The lesion involves the leg · the photo was captured at an angle:
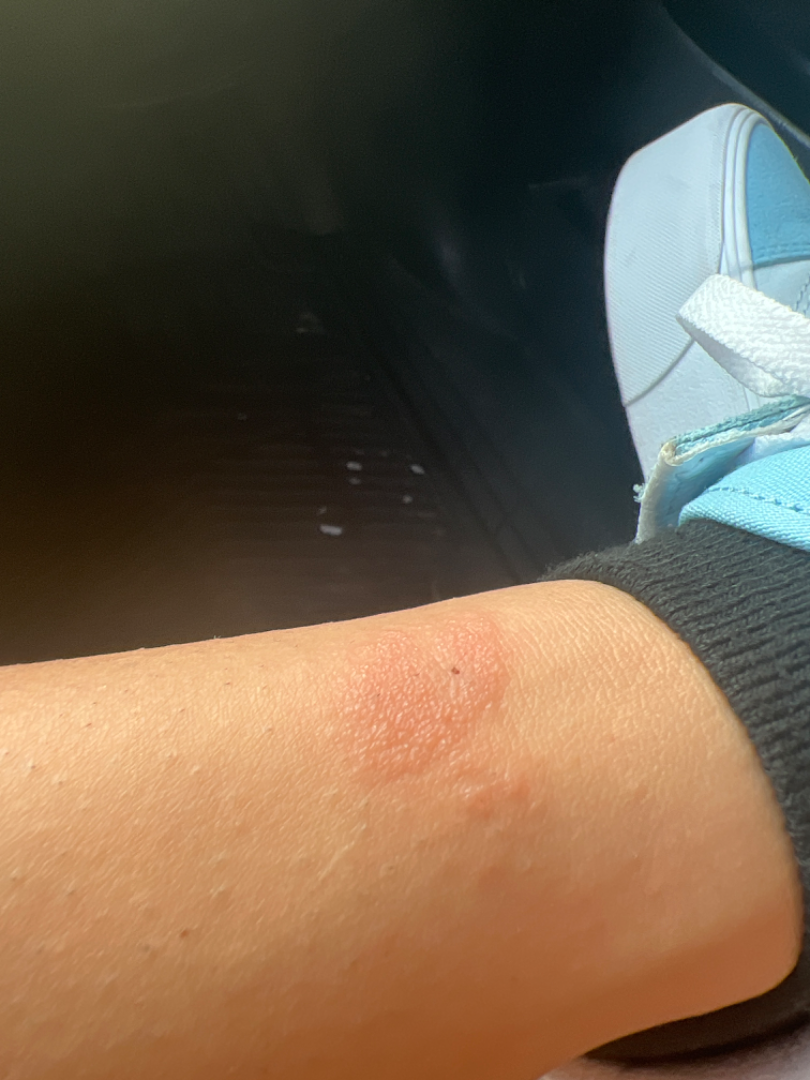present for=less than one week
self-categorized as=a rash
reported symptoms=itching
assessment=reviewed remotely by one dermatologist: the primary impression is Insect Bite; with consideration of SK/ISK; possibly Eczema